Present for more than one year. A close-up photograph. Female contributor, age 18–29:
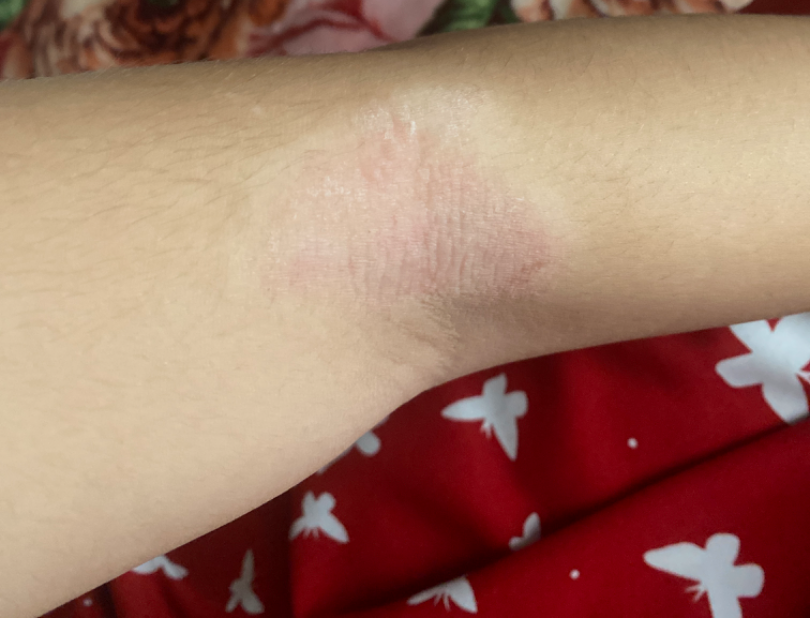On photographic review, Eczema (primary); Psoriasis (considered).